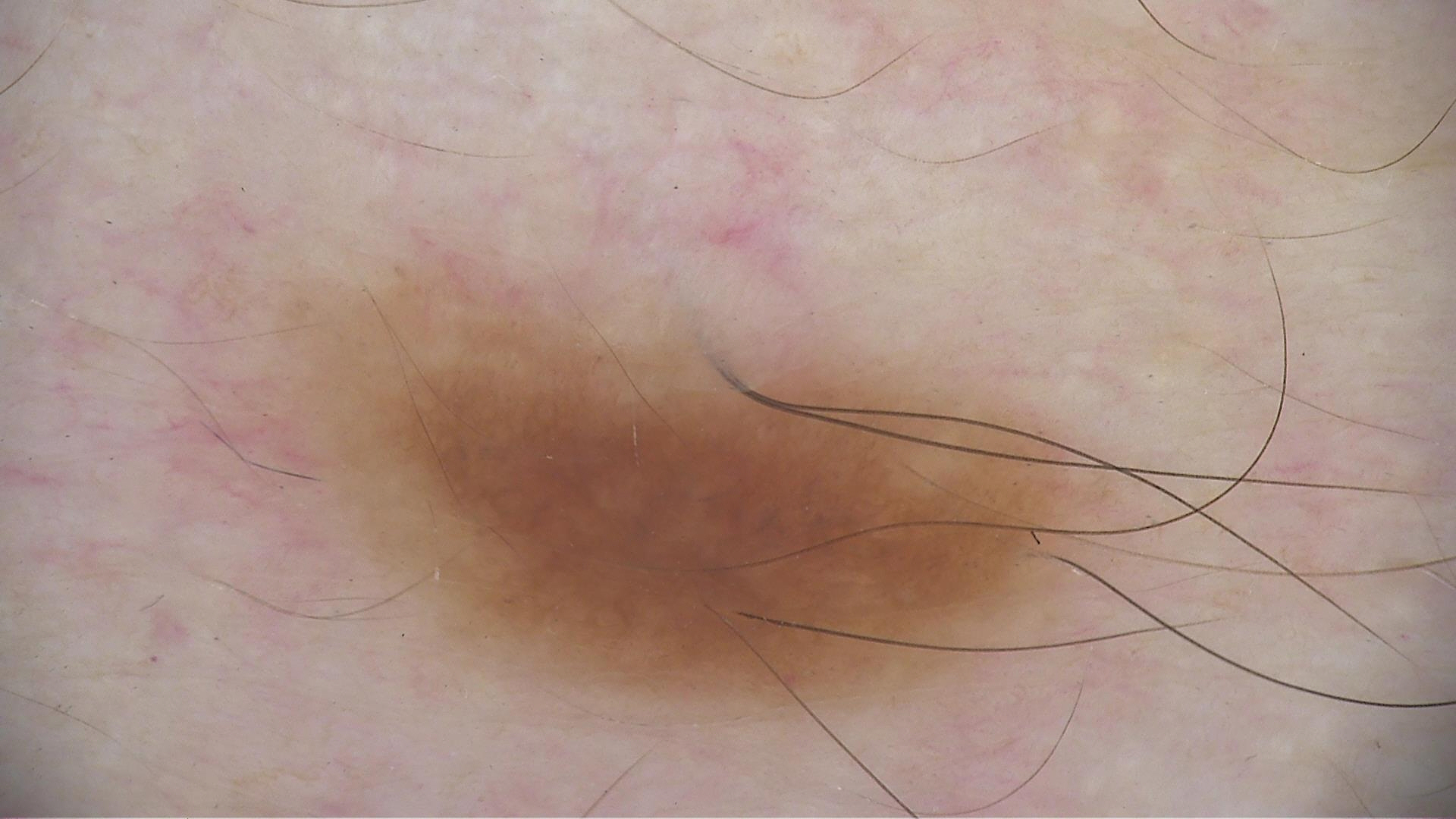| feature | finding |
|---|---|
| diagnostic label | dysplastic junctional nevus (expert consensus) |